The lesion involves the leg. This image was taken at an angle:
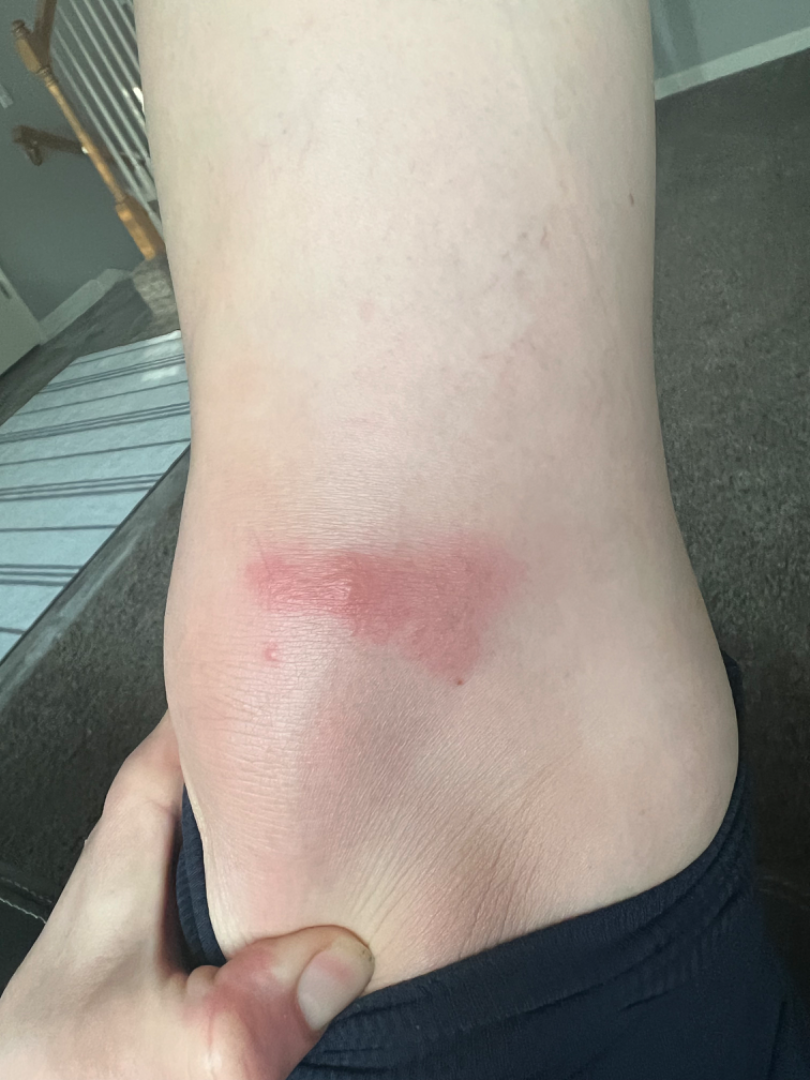assessment=could not be assessed.